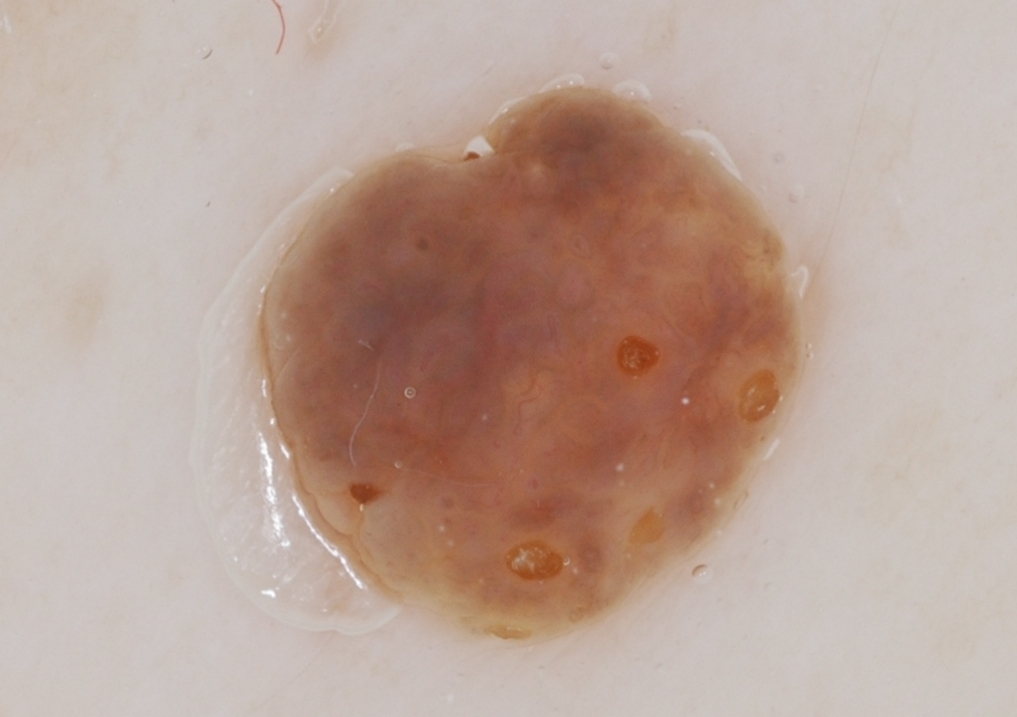| field | value |
|---|---|
| patient | male, roughly 60 years of age |
| image | dermoscopy |
| dermoscopic findings | milia-like cysts; absent: streaks, pigment network, and negative network |
| bounding box | box(247, 85, 810, 644) |
| lesion size | ~31% of the field |
| impression | a seborrheic keratosis |